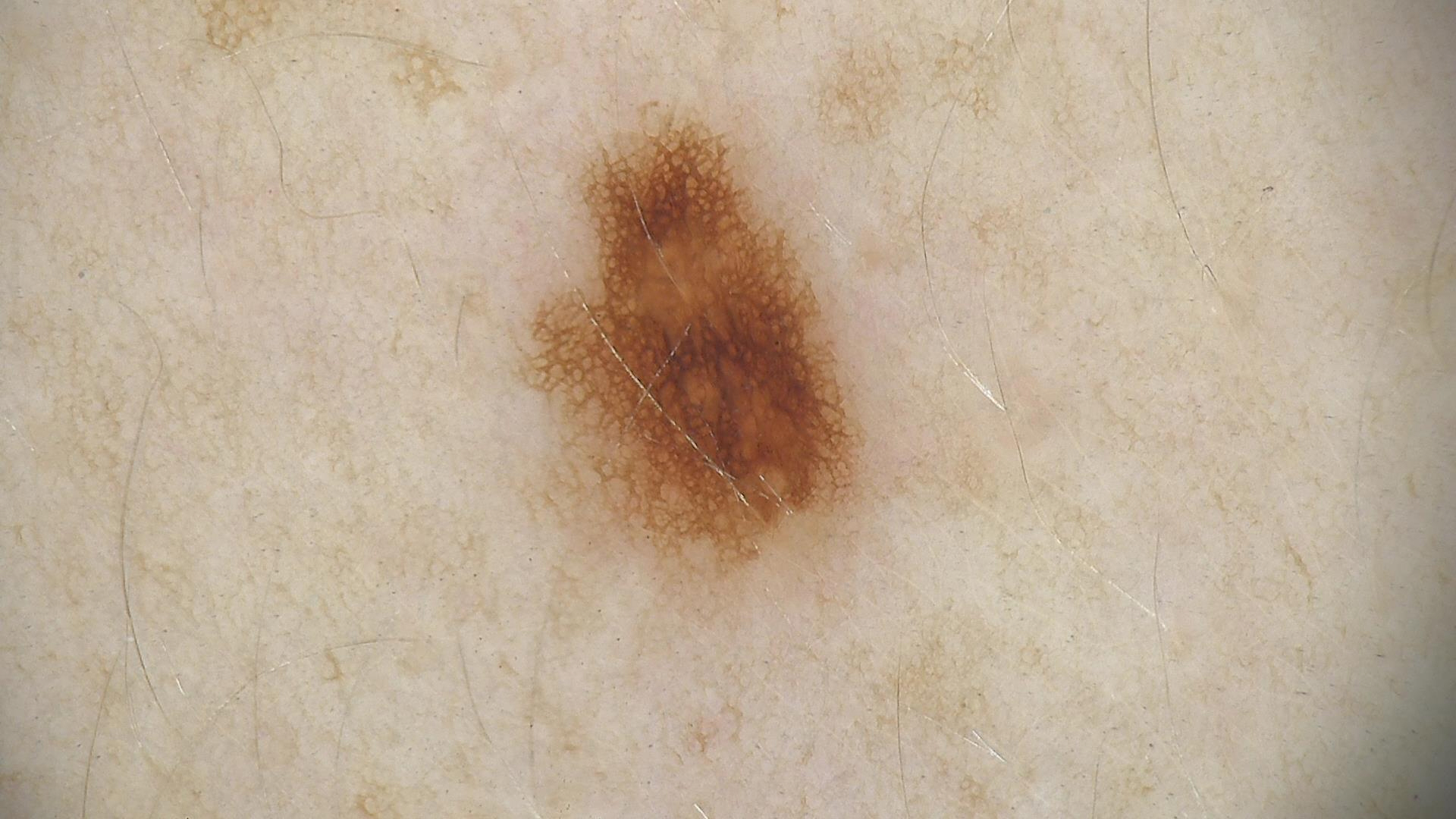A skin lesion imaged with a dermatoscope.
Classified as a benign lesion — a dysplastic junctional nevus.